A dermoscopy image of a single skin lesion:
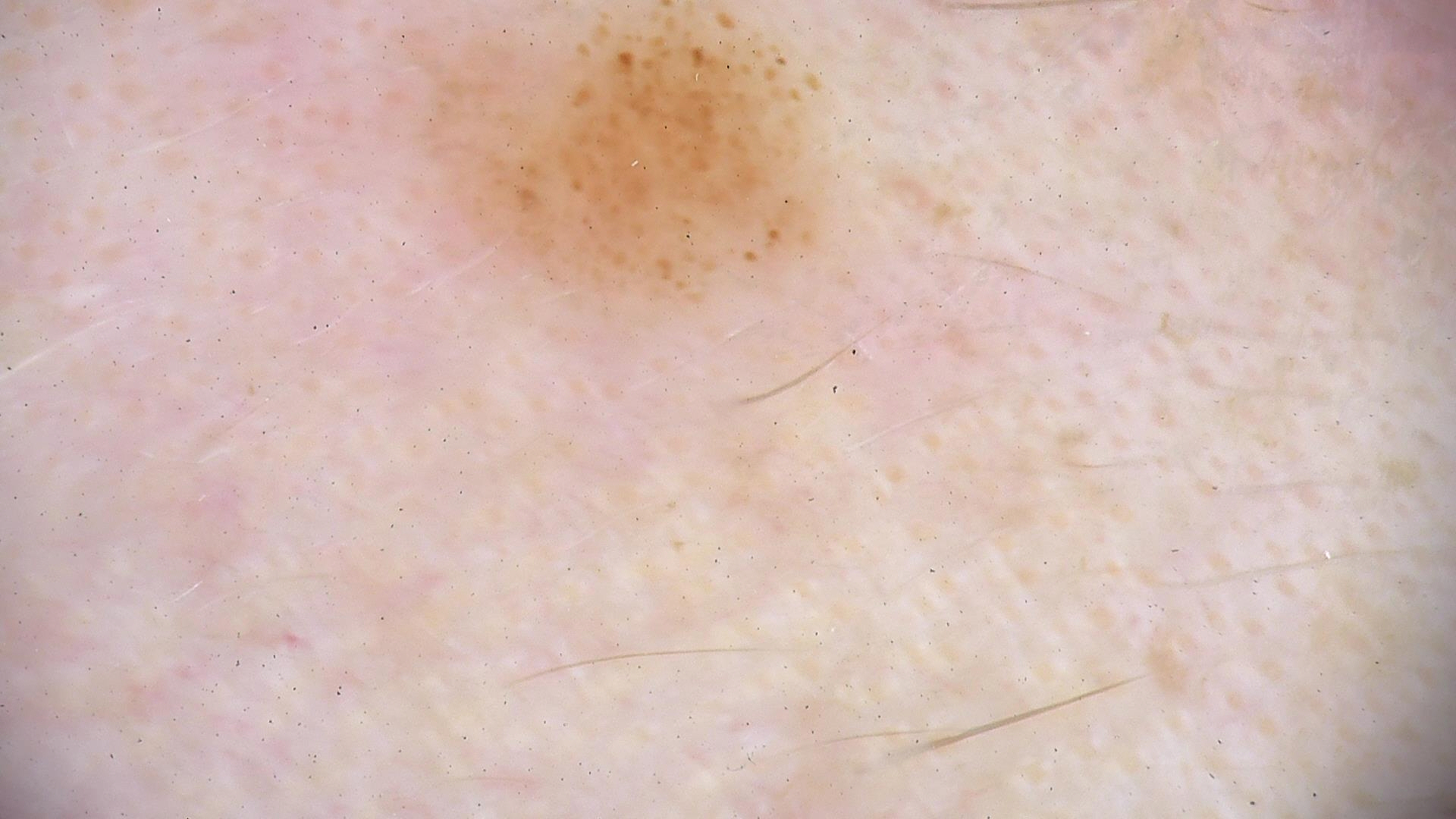The morphology is that of a banal lesion.
The diagnostic label was a compound nevus.